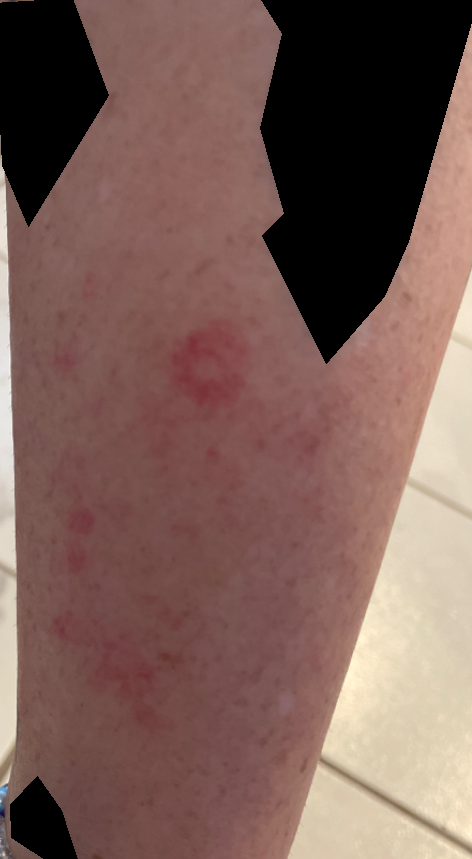body_site: leg
patient: female, age 40–49
shot_type: at an angle
differential:
  leading:
    - Allergic Contact Dermatitis
  considered:
    - Insect Bite
  unlikely:
    - Eczema